This is a close-up image.
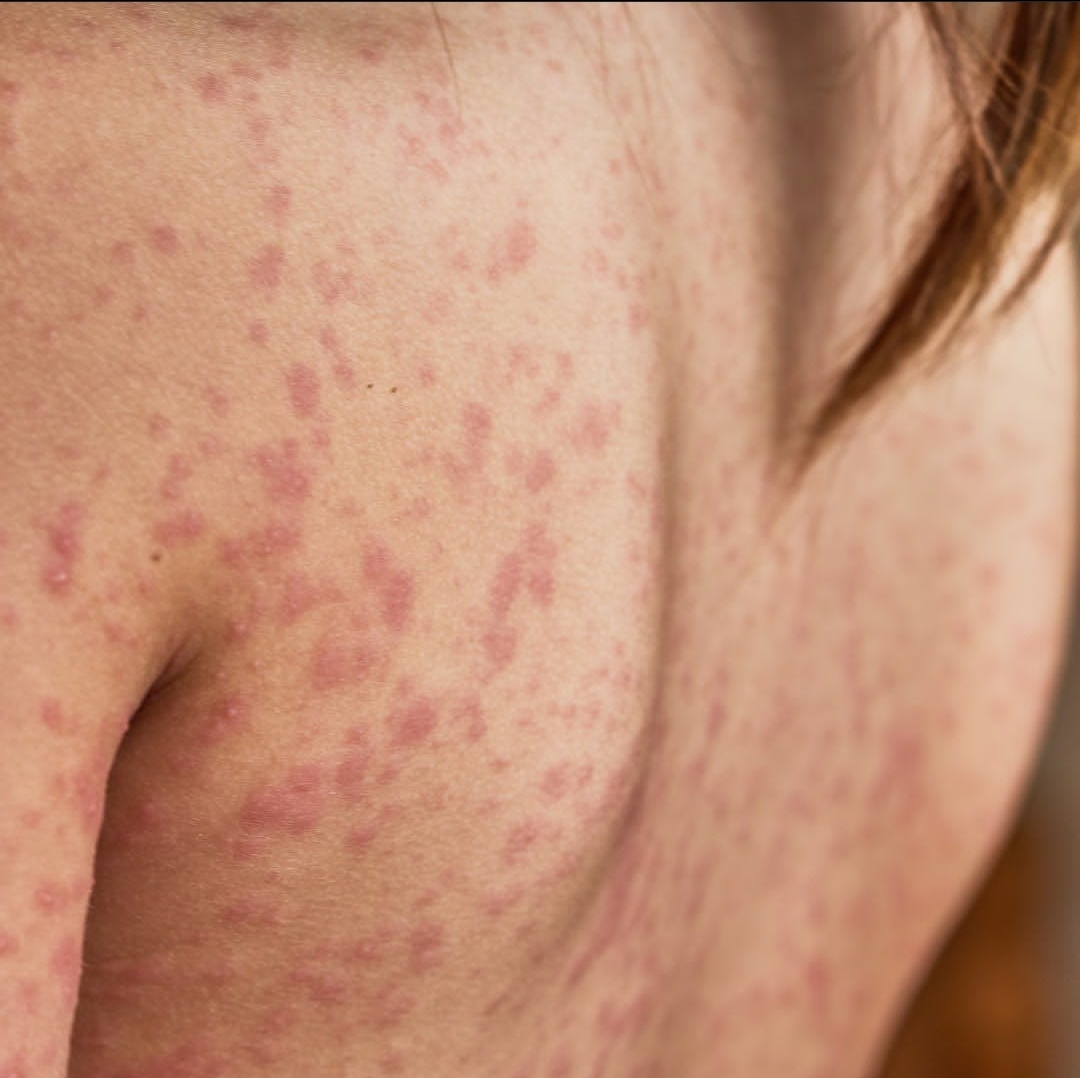On teledermatology review: the impression was split between Viral Exanthem and Drug Rash.